A clinical photograph of a skin lesion; recorded as Fitzpatrick II; a male patient in their 80s; the chart records prior malignancy (patient or family), prior skin cancer (patient or family), and no pesticide exposure: 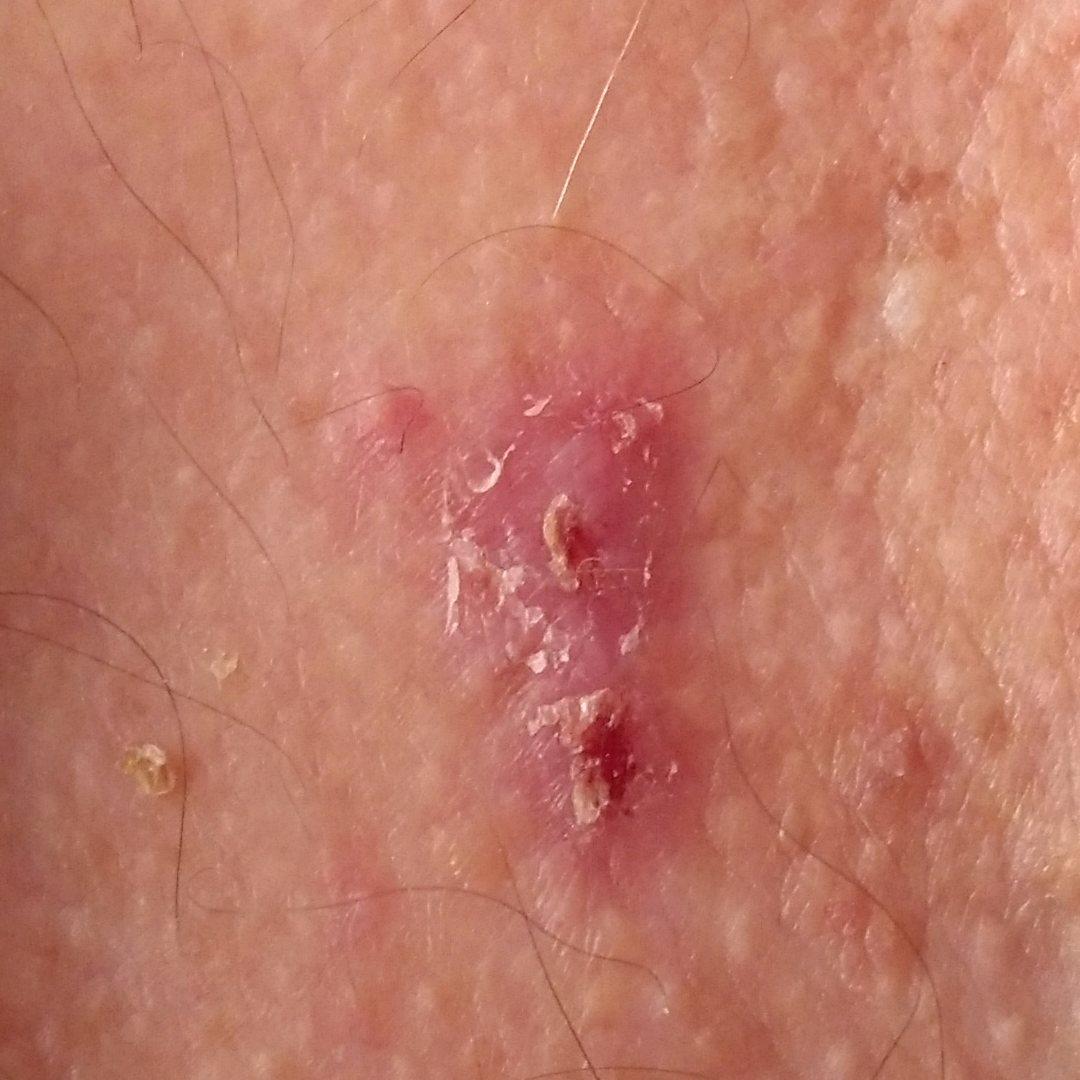Case:
– body site · the chest
– size · 20 × 10 mm
– diagnosis · basal cell carcinoma (biopsy-proven)